Symptoms reported: bothersome appearance; the lesion is described as raised or bumpy; reported duration is one to four weeks; the subject is a female aged 30–39; self-categorized by the patient as a rash; located on the back of the hand; this is a close-up image:
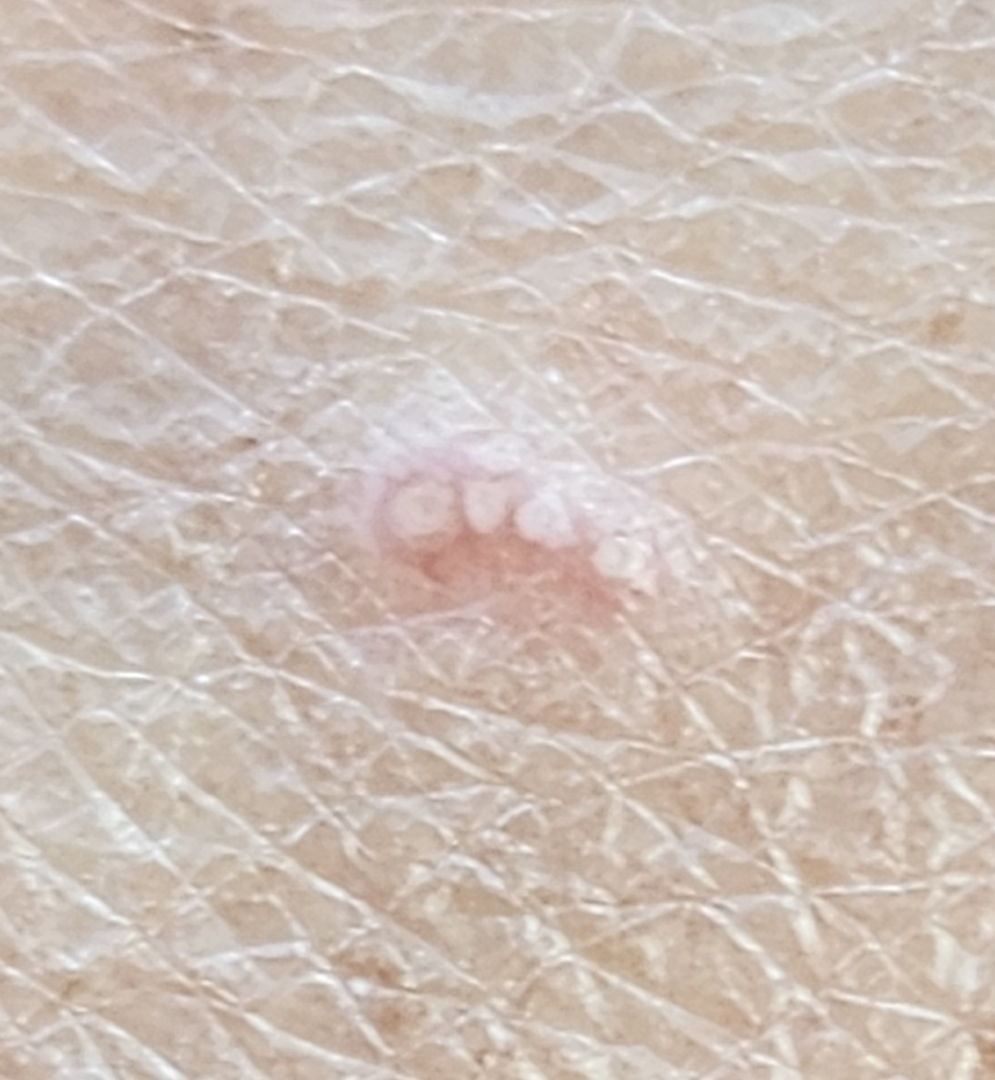Most consistent with Actinic Keratosis.